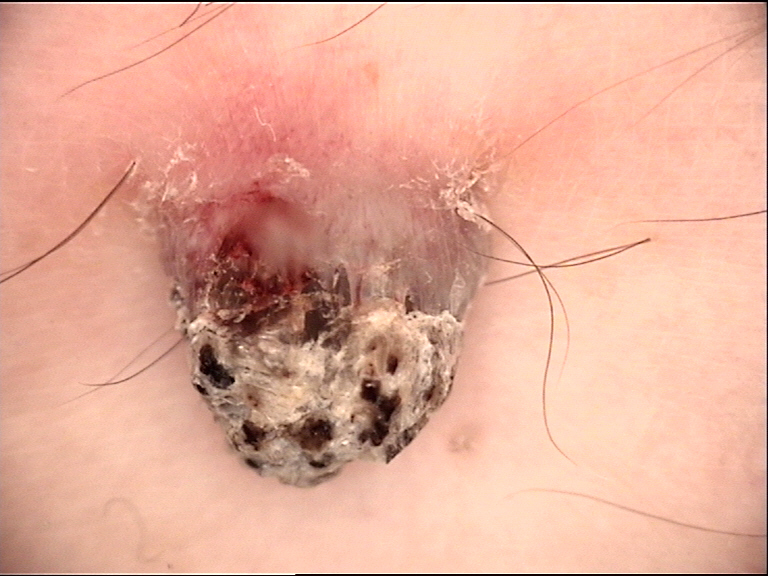Case:
Dermoscopy of a skin lesion. The morphology is that of a keratinocytic lesion.
Diagnosis:
Biopsy-confirmed as a cutaneous horn.